Close-up view · located on the top or side of the foot — 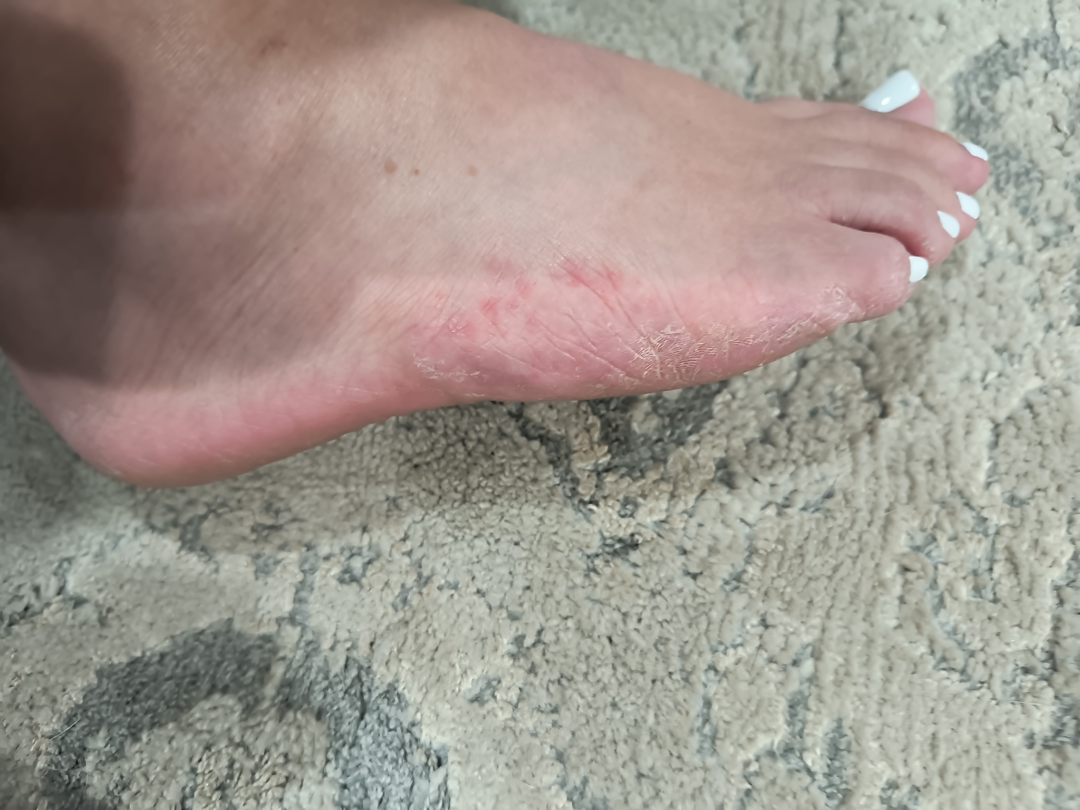<summary>
<texture>flat</texture>
<symptoms>none reported</symptoms>
<differential>
  <leading>Tinea</leading>
</differential>
</summary>